A dermoscopy image of a single skin lesion.
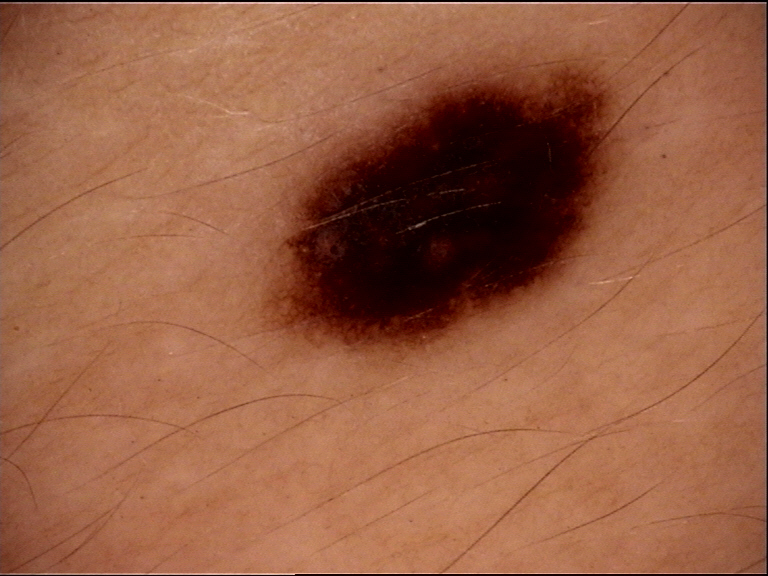The diagnosis was a benign lesion — a dysplastic junctional nevus.